A dermatoscopic image of a skin lesion: 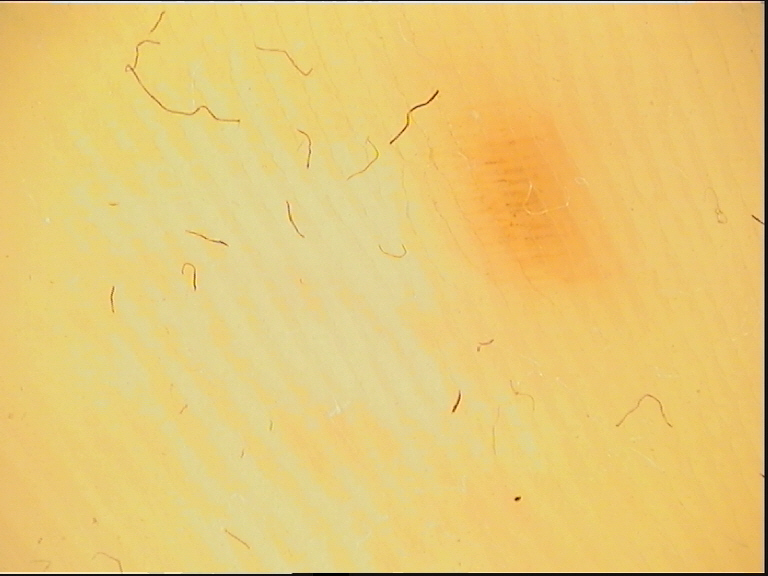diagnosis: acral dysplastic junctional nevus (expert consensus)